The head or neck is involved · this is a close-up image: 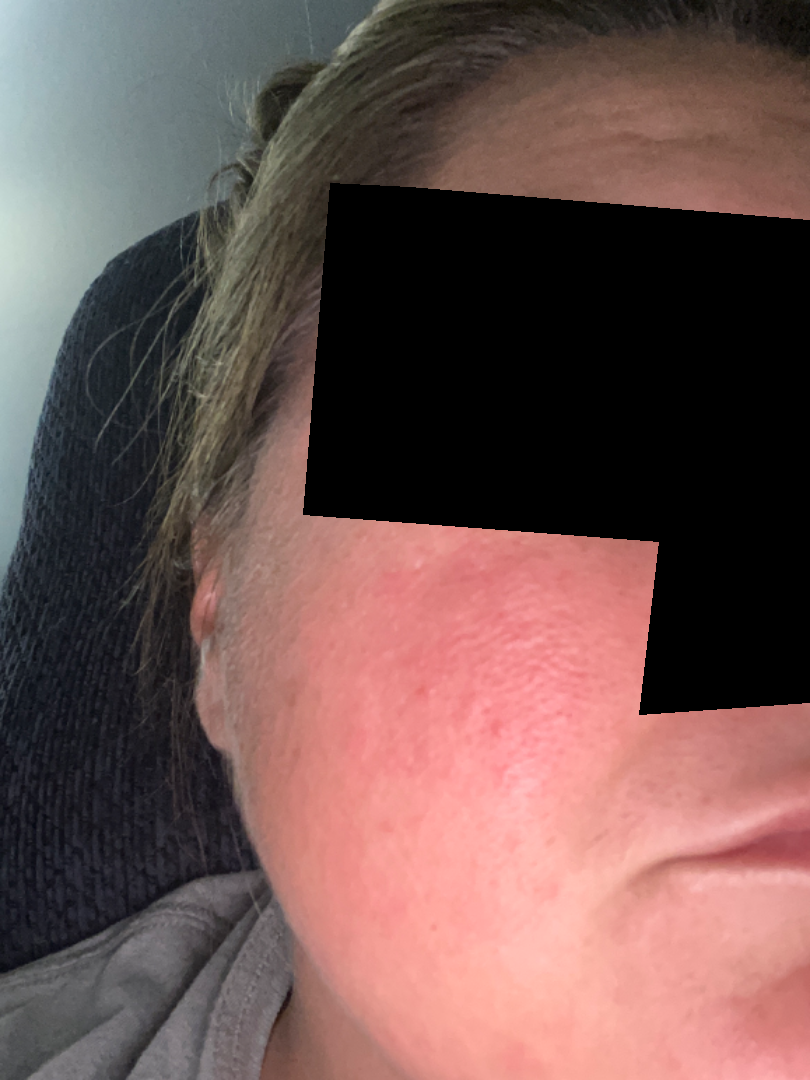- impression: the differential is split between Rosacea and Flushing; less likely is Cutaneous lupus